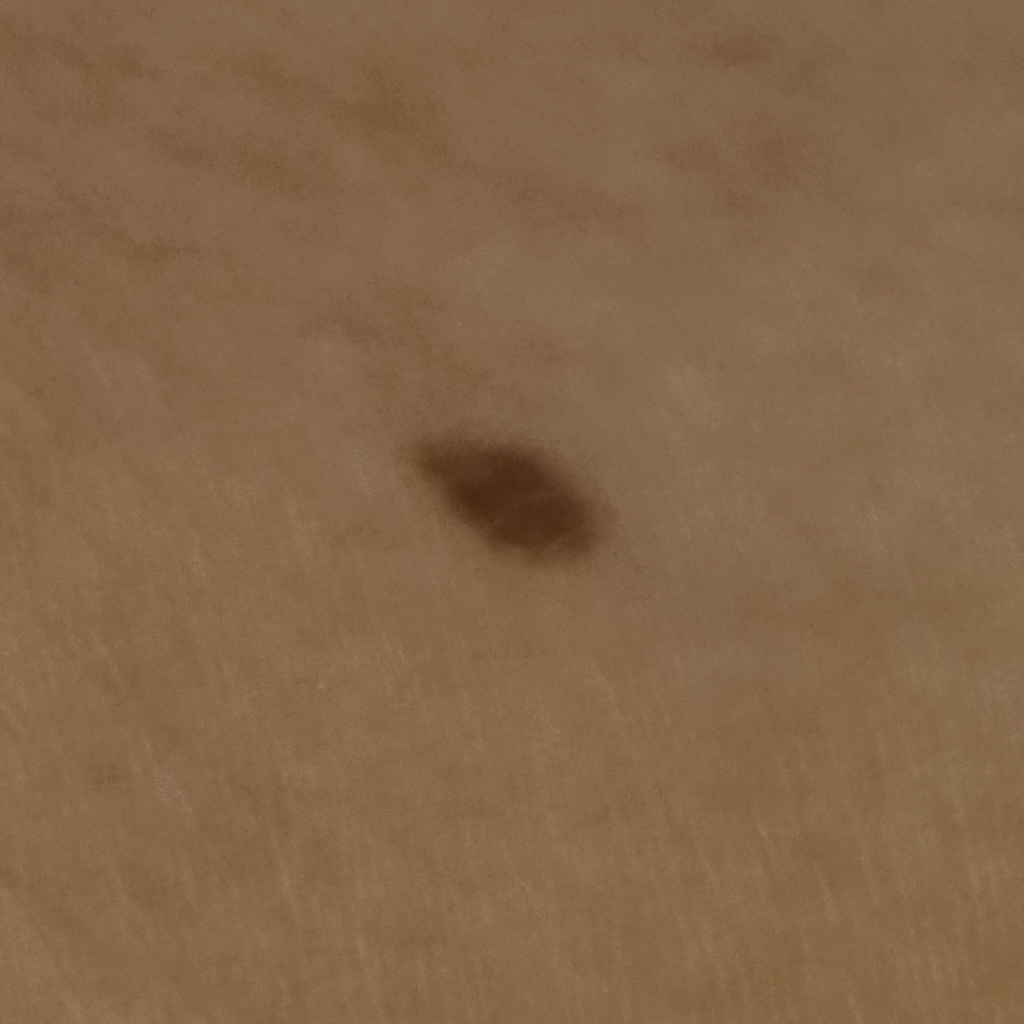Collected as part of a research study, without a referral diagnosis.
A female subject age 60.
A macroscopic clinical photograph of a skin lesion.
The lesion is located on the torso.
The lesion measures approximately 6.2 mm.
The diagnostic impression was a seborrheic keratosis.